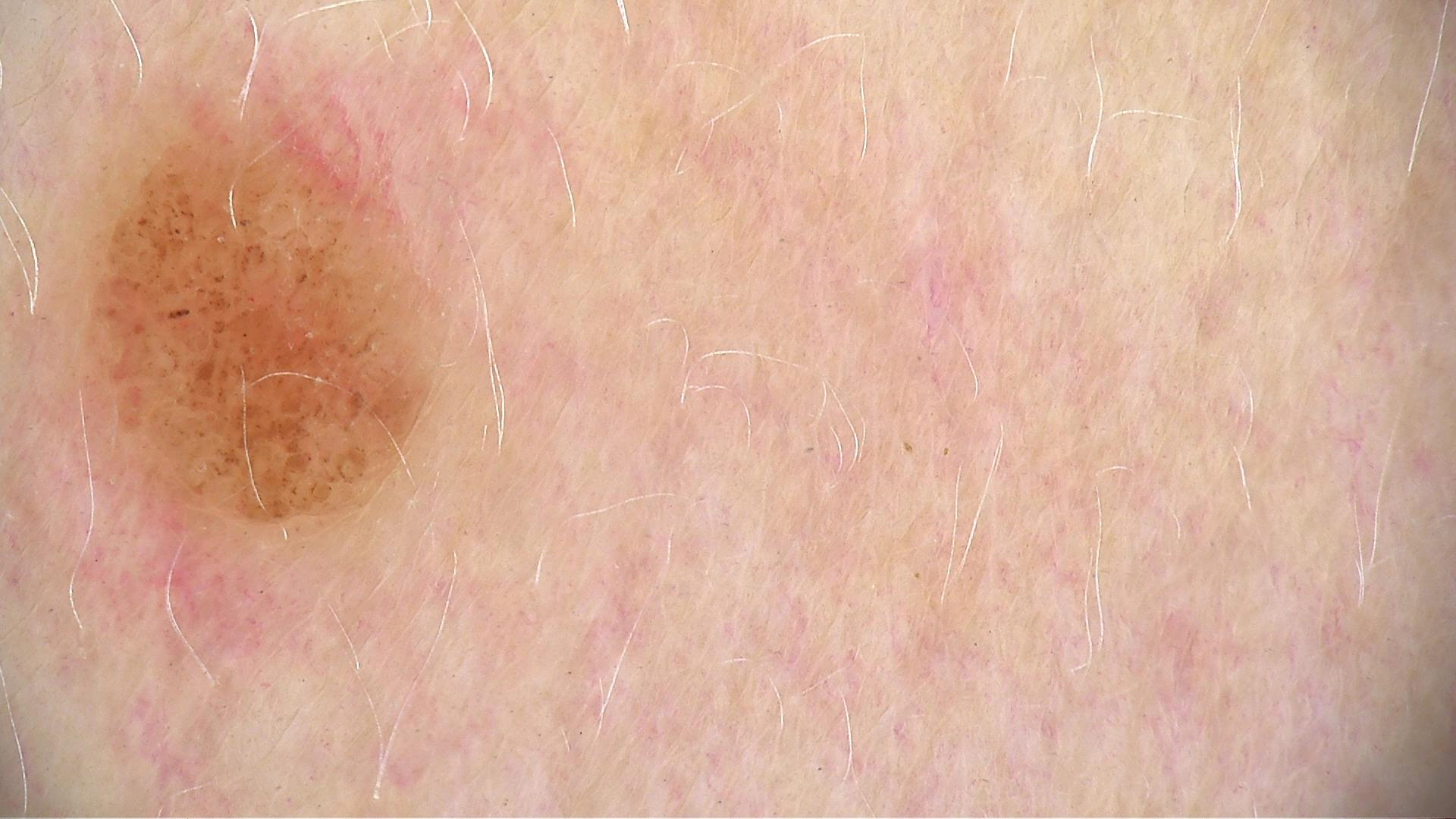image = dermatoscopy
category = banal
assessment = compound nevus (expert consensus)